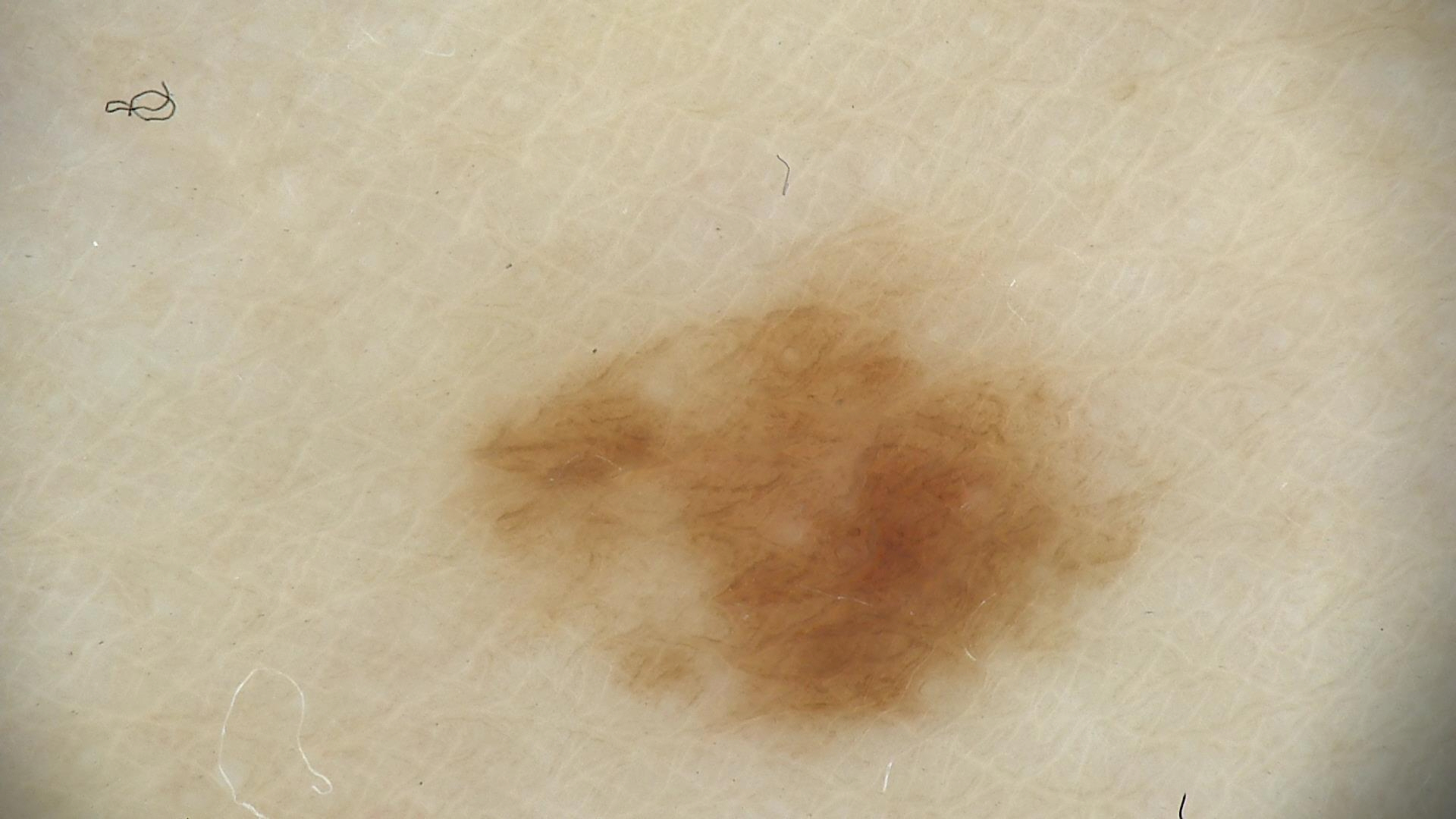diagnostic label = dysplastic junctional nevus (expert consensus)